The photograph was taken at an angle. Located on the arm:
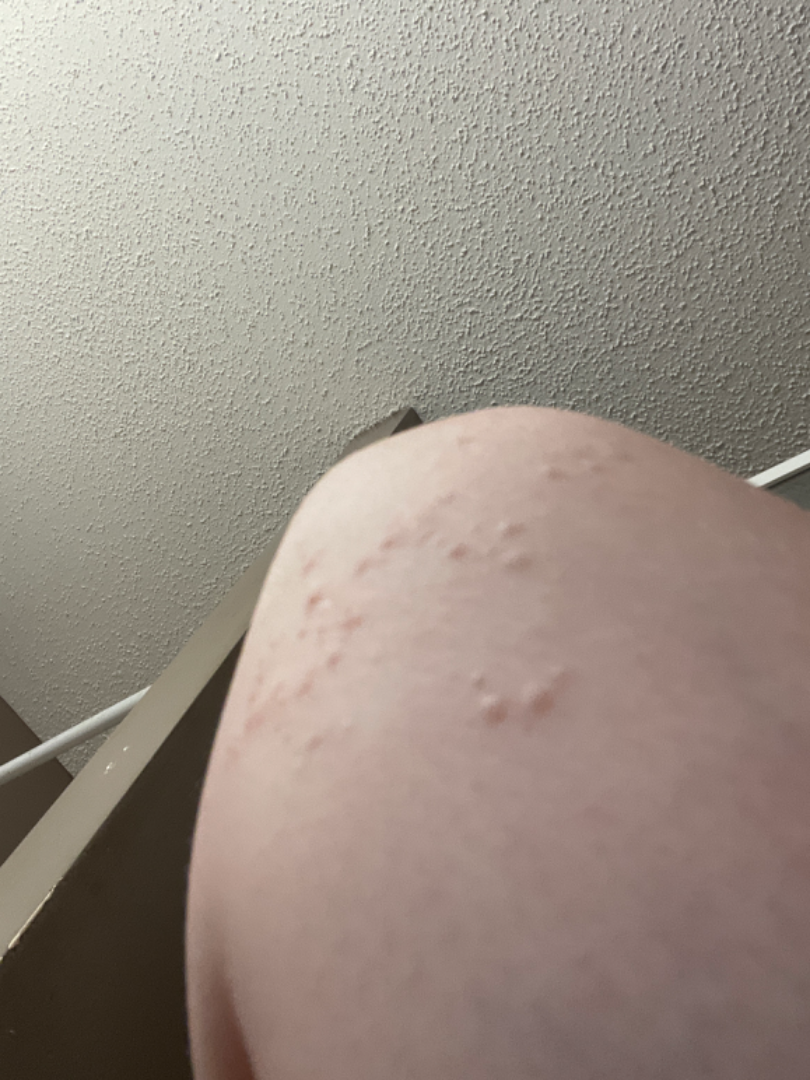Assessment:
The reviewing dermatologist was unable to assign a differential diagnosis from the image.
Clinical context:
No relevant lesion symptoms reported. No constitutional symptoms were reported. The patient notes the lesion is raised or bumpy. Skin tone: Fitzpatrick skin type II. The patient described the issue as a rash.